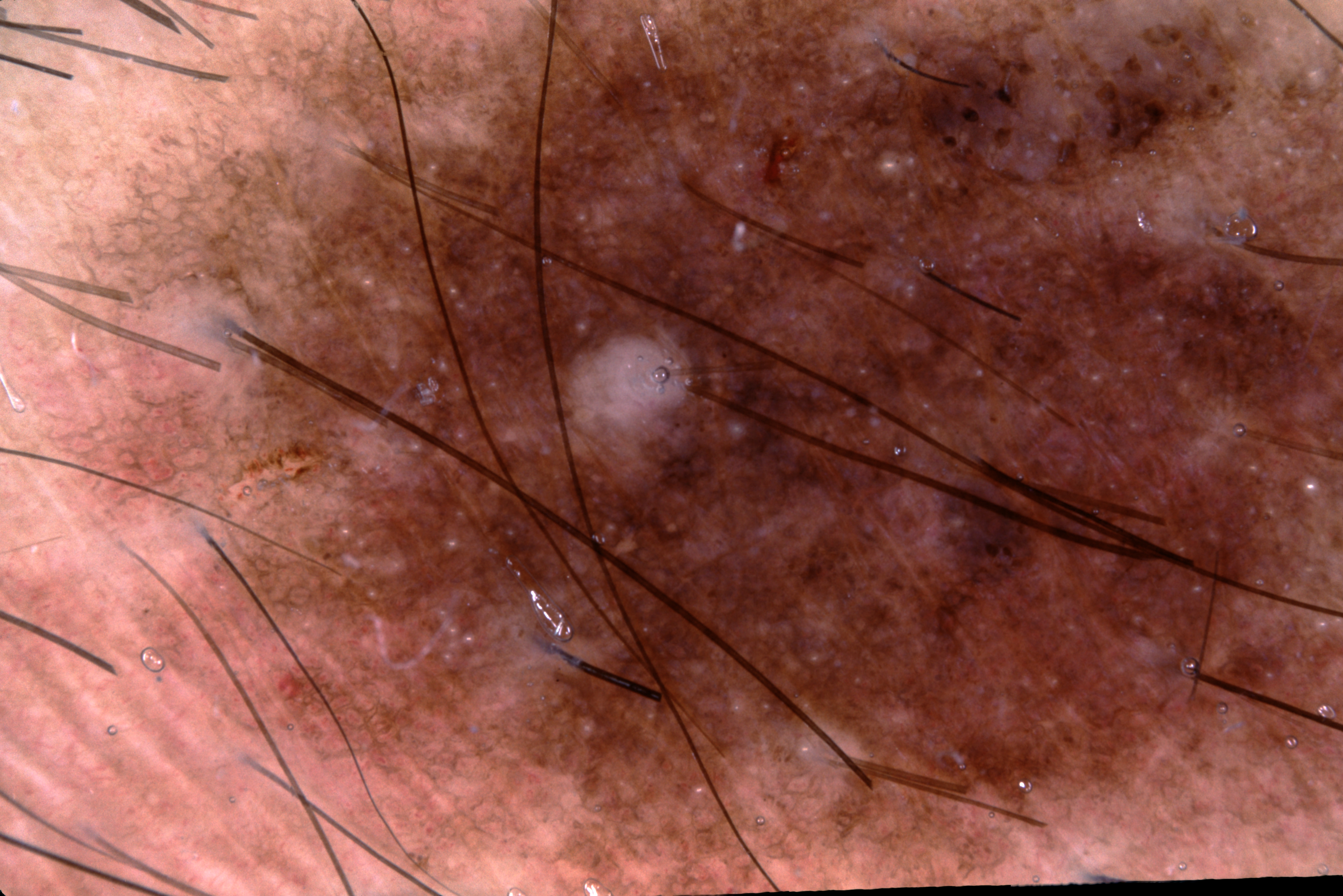subject = male, aged around 65
image = dermoscopic image
lesion location = extends across the entire field of view
dermoscopic features = milia-like cysts and pigment network
diagnosis = a melanocytic nevus, a benign skin lesion